A dermoscopy image of a single skin lesion.
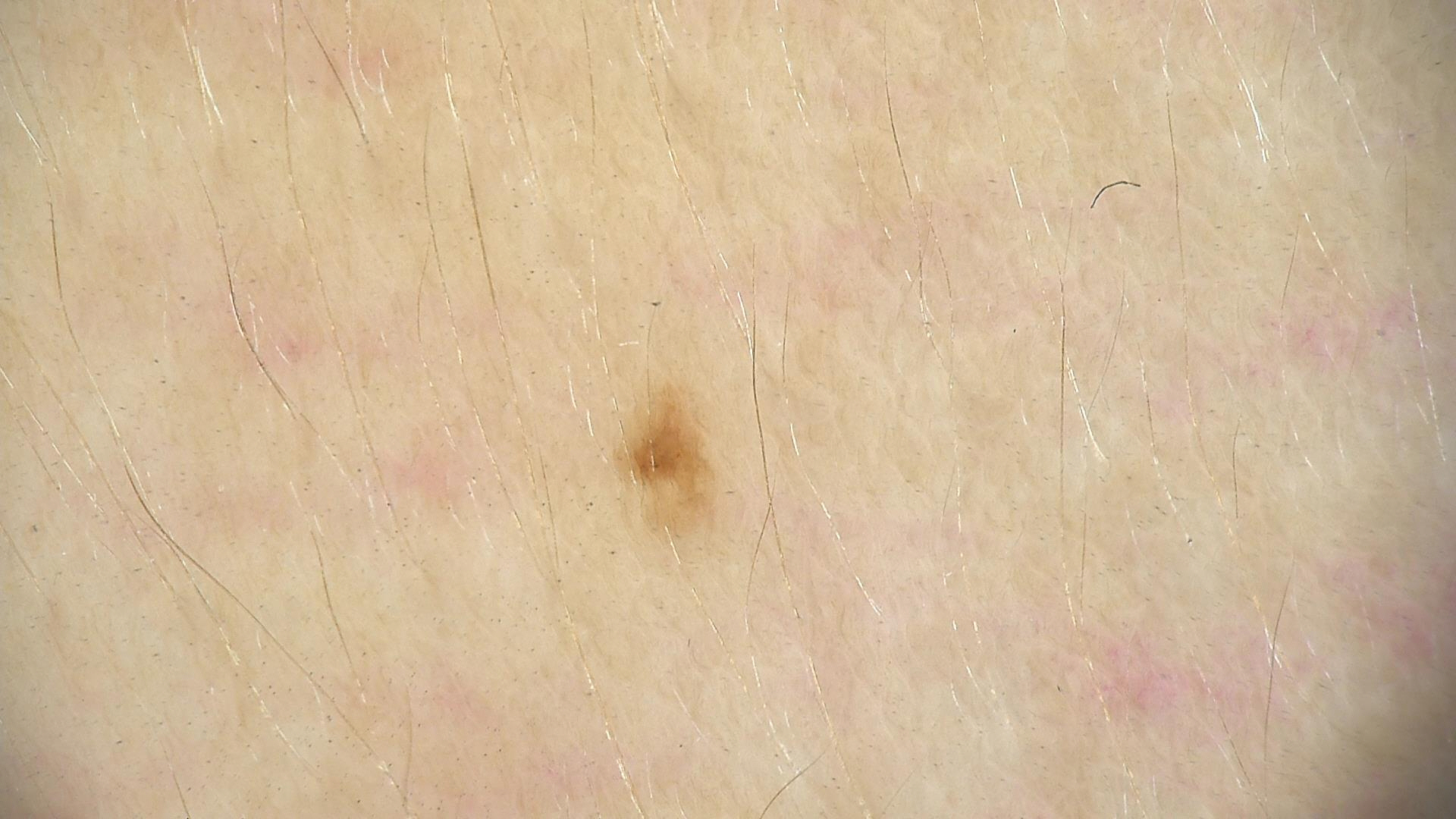Case:
* diagnostic label · junctional nevus (expert consensus)